Located on the head or neck and front of the torso. The contributor is 18–29, female. The photo was captured at a distance: 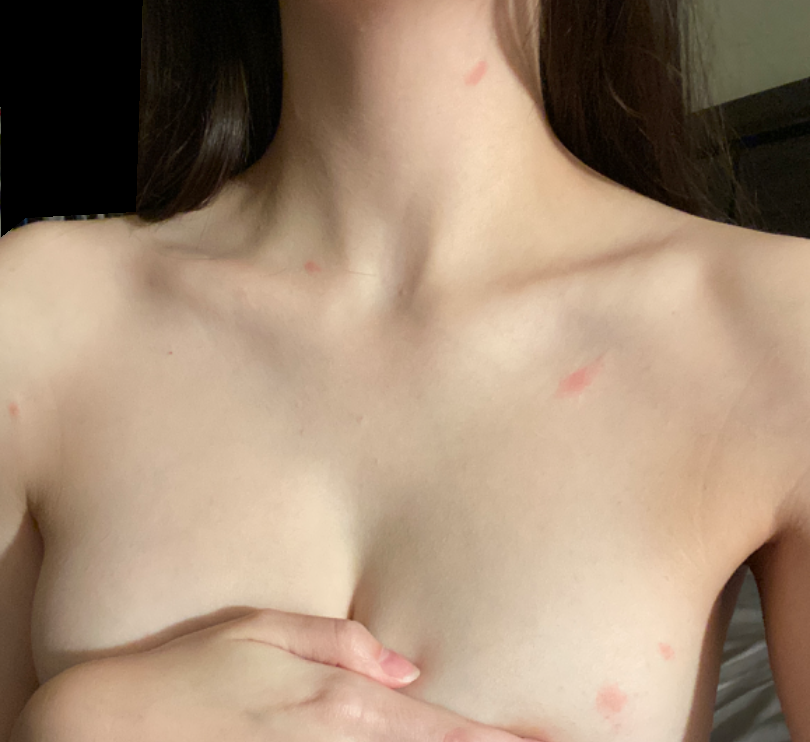assessment: indeterminate from the photograph
duration: less than one week
texture:
  - raised or bumpy
  - rough or flaky